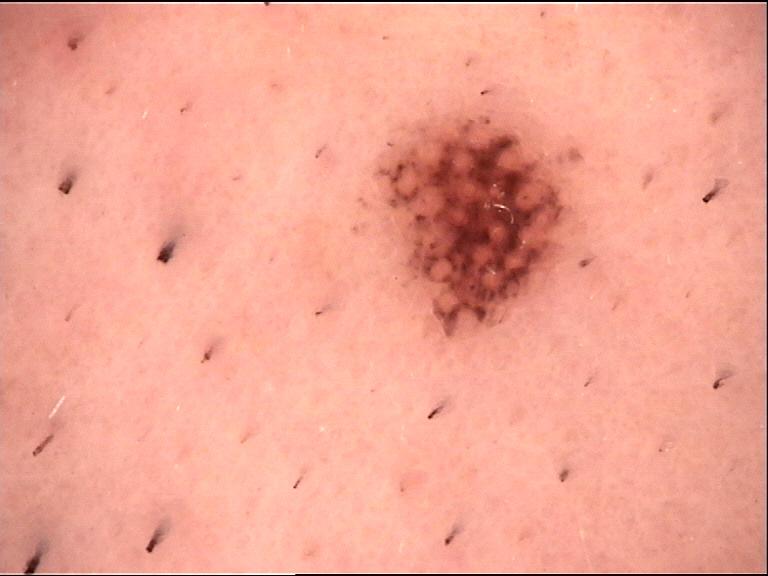A dermoscopic photograph of a skin lesion.
Consistent with a compound lesion — a Miescher nevus.